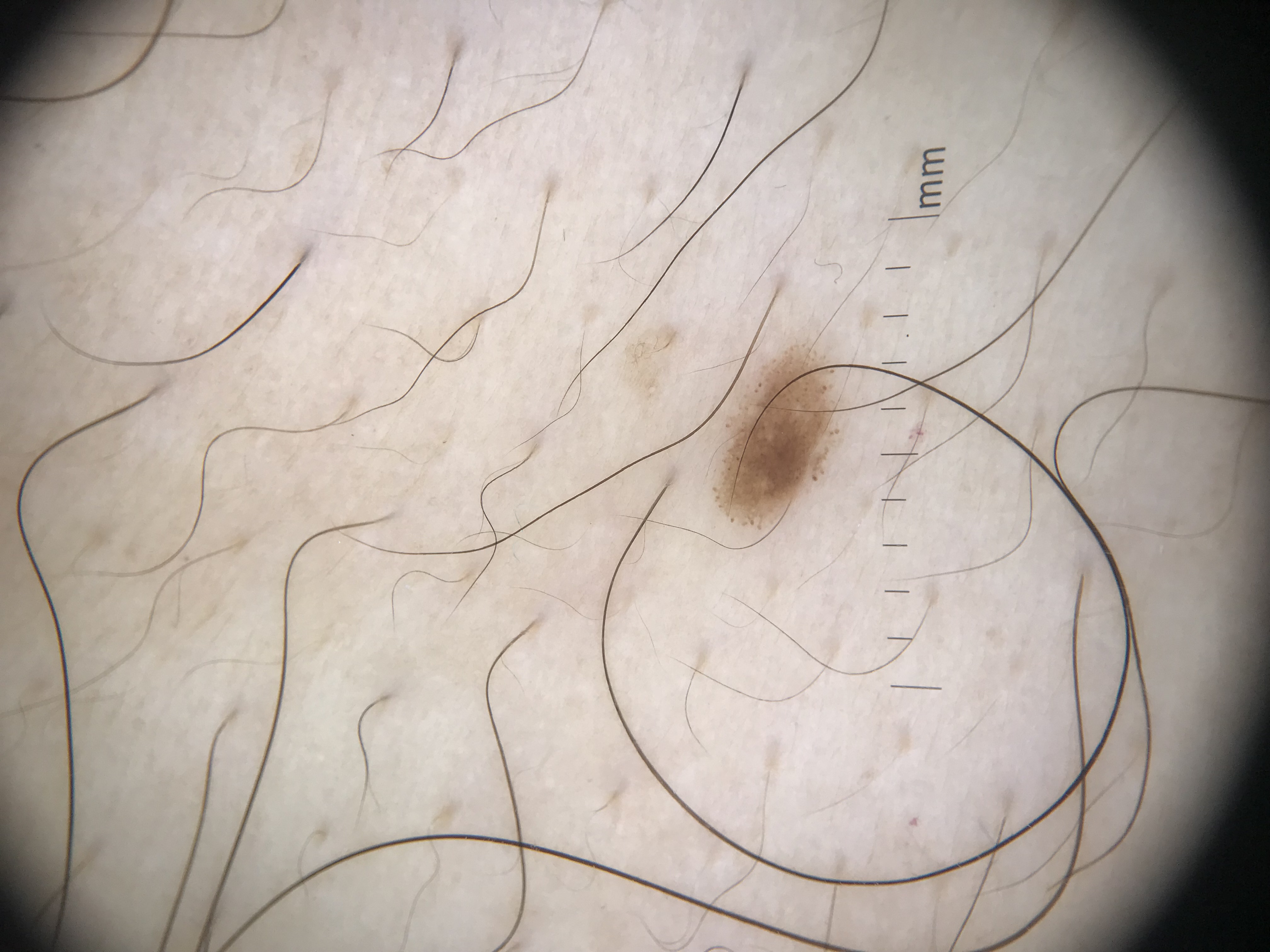class = dysplastic junctional nevus (expert consensus).